A clinical photograph showing a skin lesion: 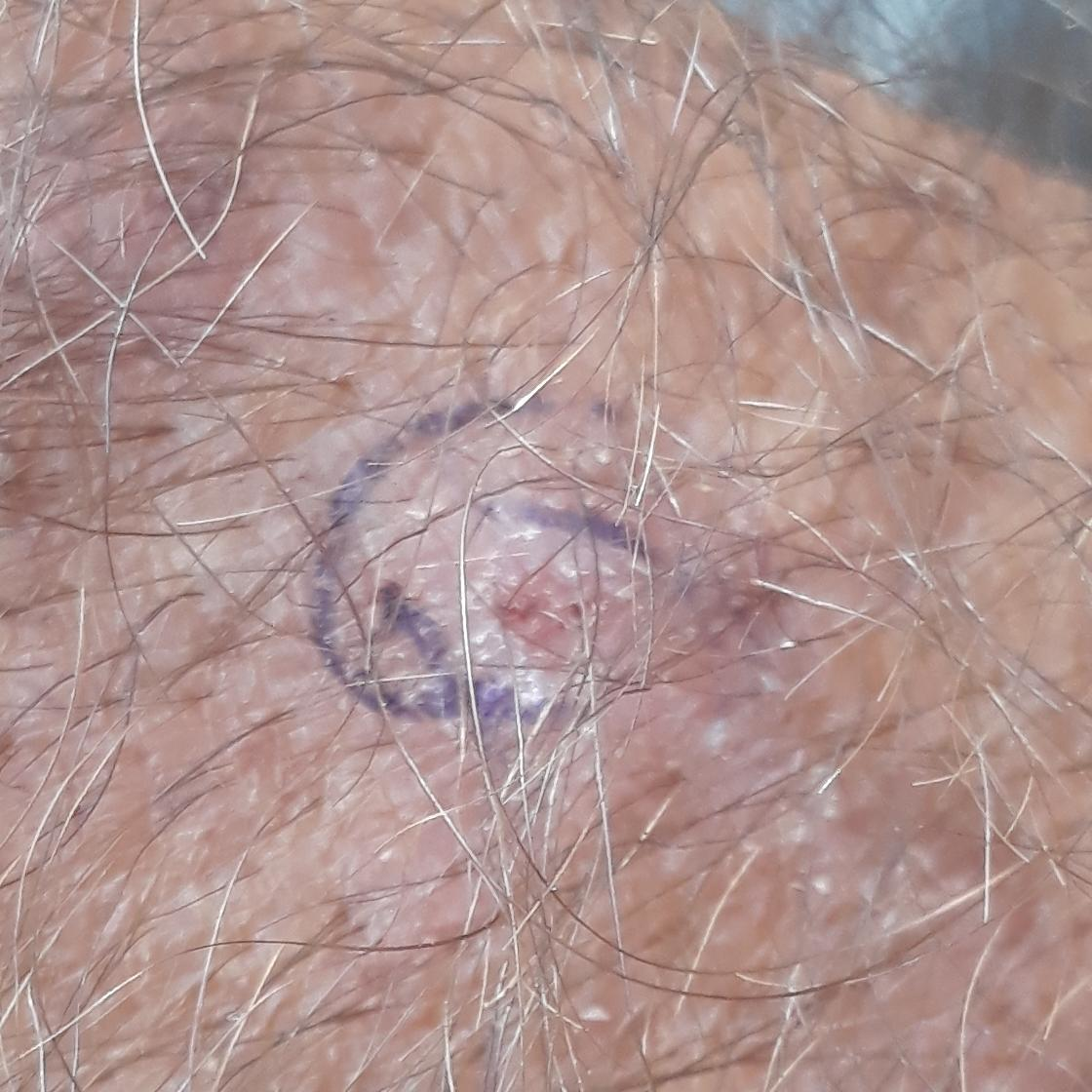The lesion was found on a forearm.
The patient reports that the lesion itches, but does not hurt and has not bled.
Consistent with an actinic keratosis.